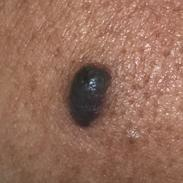The diagnostic impression was a nevus.